The patient is 30–39, female. Skin tone: FST I. The contributor notes the condition has been present for less than one week. The contributor notes the lesion is fluid-filled and raised or bumpy. Located on the arm. The photograph was taken at an angle. The patient described the issue as a rash. The contributor notes associated fatigue. The contributor notes enlargement, pain, itching and burning:
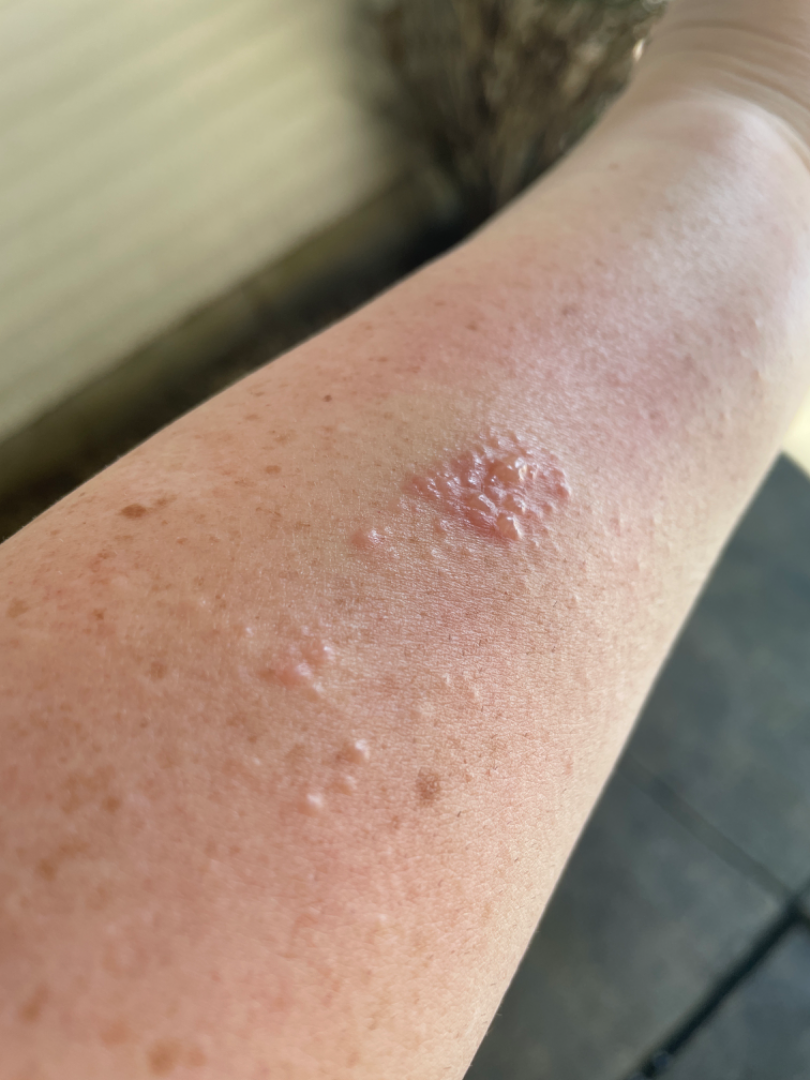On dermatologist assessment of the image: Herpes Simplex (weight 0.39); Allergic Contact Dermatitis (weight 0.27); Herpes Zoster (weight 0.25); Lymphangioma (weight 0.09).